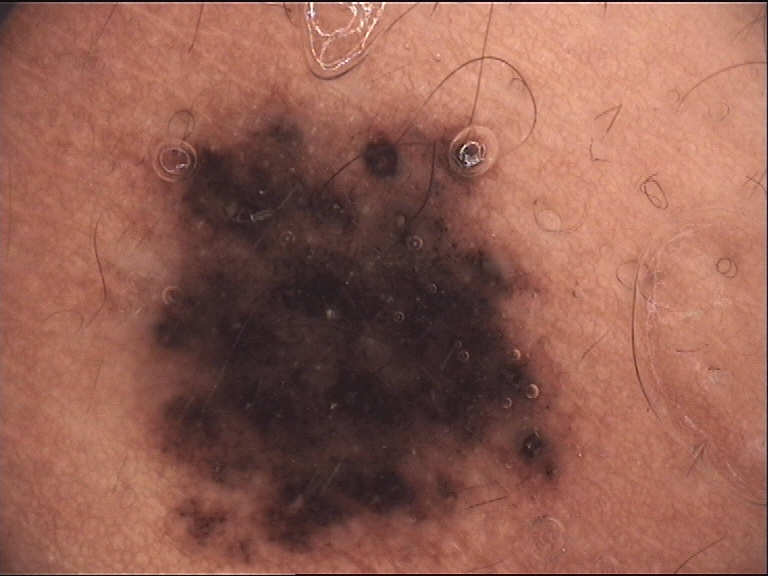A skin lesion imaged with a dermatoscope. Labeled as a congenital dysplastic compound nevus.